A dermatoscopic image of a skin lesion: 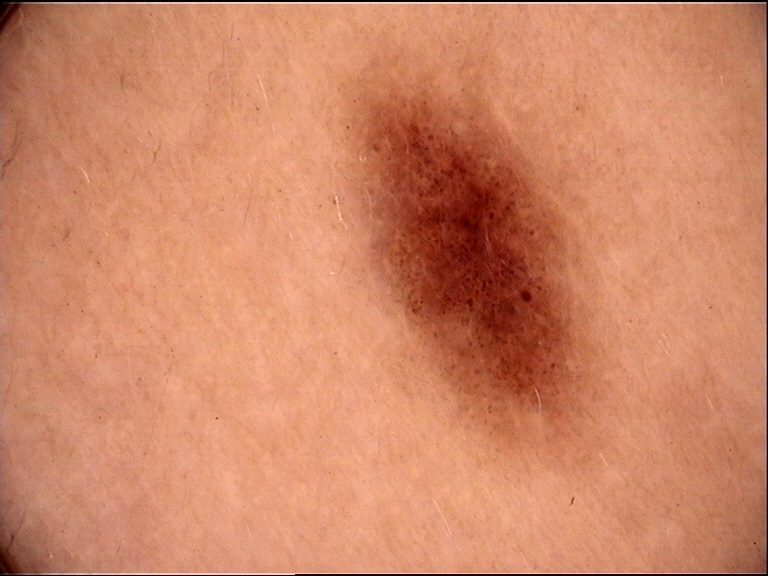| key | value |
|---|---|
| diagnostic label | dysplastic junctional nevus (expert consensus) |